Present for less than one week; texture is reported as raised or bumpy and fluid-filled; the patient is 40–49, female; an image taken at a distance; the patient considered this a rash:
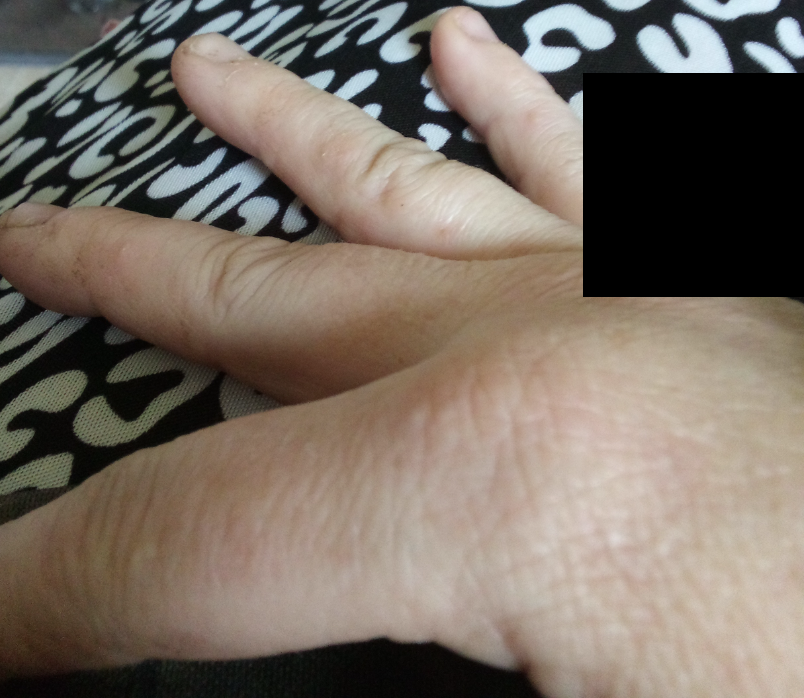Most likely Eczema; an alternative is Scabies.